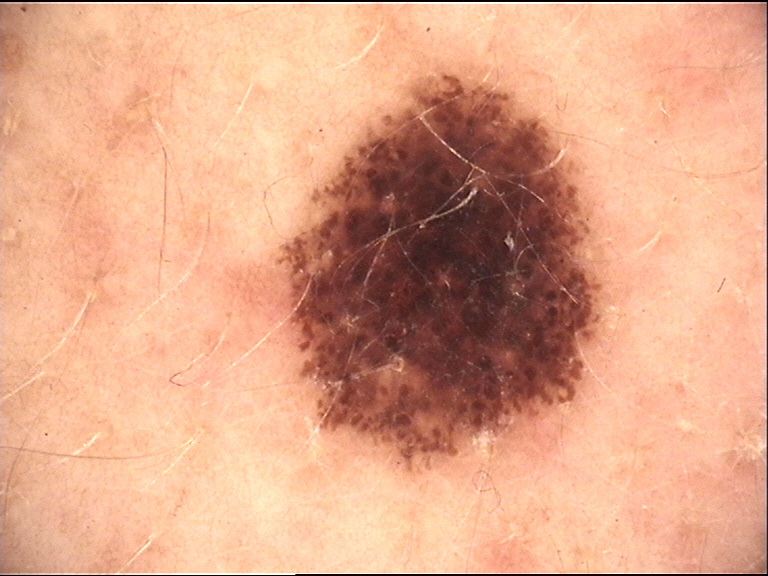| field | value |
|---|---|
| assessment | compound nevus (expert consensus) |